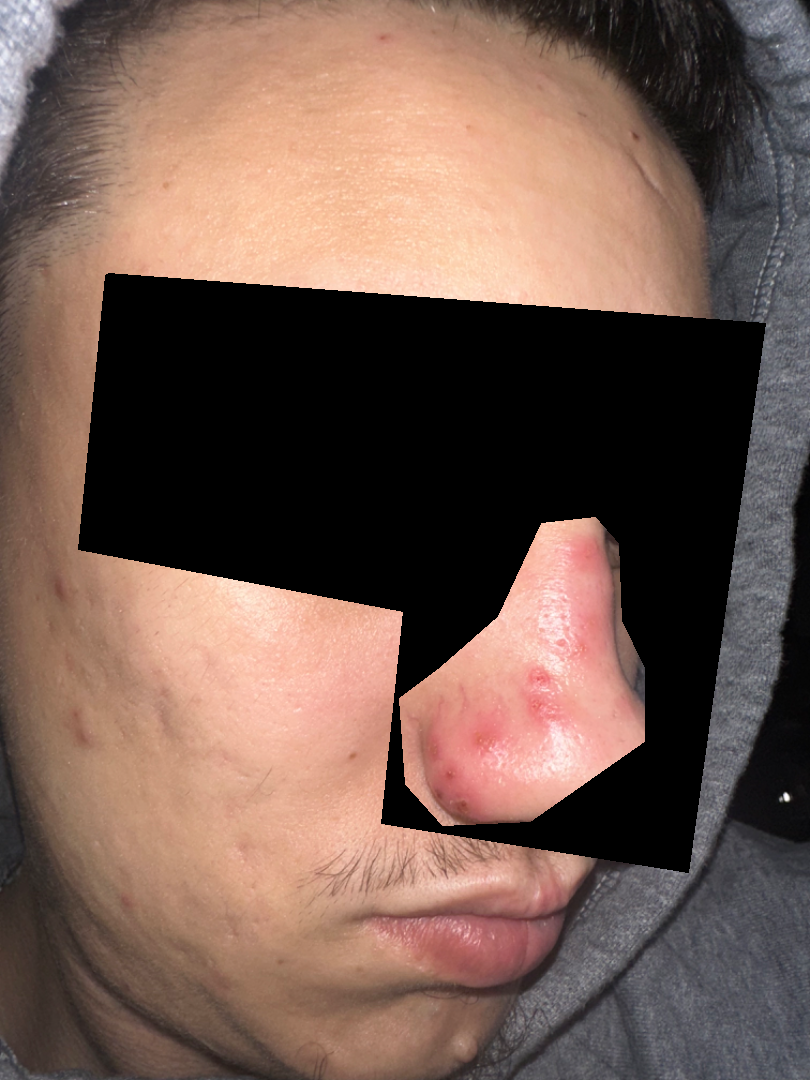skin tone=Fitzpatrick III; lay reviewers estimated MST 2 or 4 (two reviewer pools disagreed)
present for=less than one week
described texture=rough or flaky and fluid-filled
constitutional symptoms=none reported
framing=at an angle
reported symptoms=pain and itching
subject=male, age 18–29